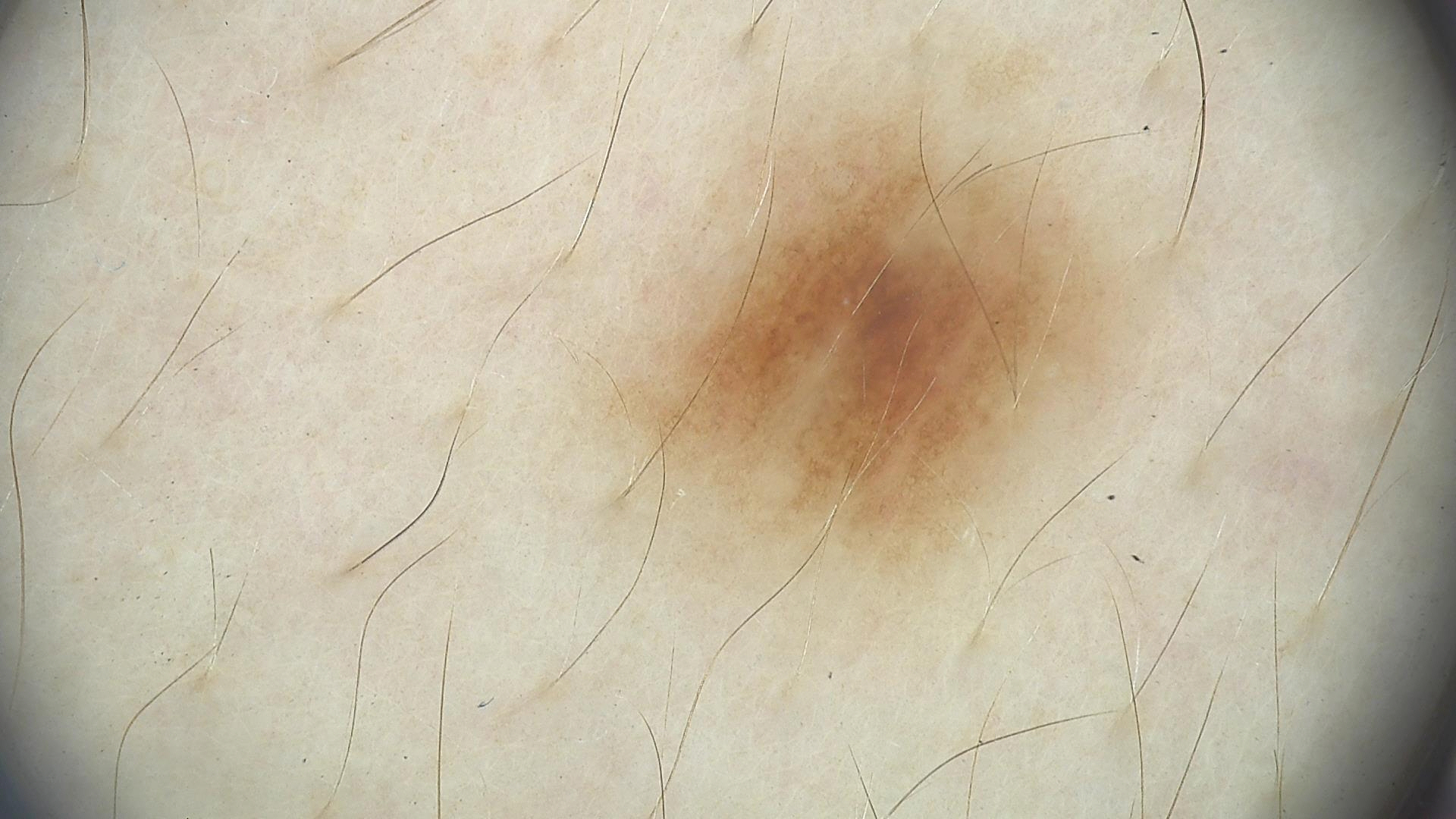Summary:
A dermoscopic photograph of a skin lesion.
Impression:
Classified as a benign lesion — a dysplastic junctional nevus.